Symptoms reported: itching · the patient reports the lesion is raised or bumpy · this is a close-up image · female contributor, age 30–39 · reported duration is less than one week · self-categorized by the patient as a rash · skin tone: lay reviewers estimated Monk skin tone scale 2 or 3 (two reviewer pools) · the affected area is the front of the torso and back of the torso: 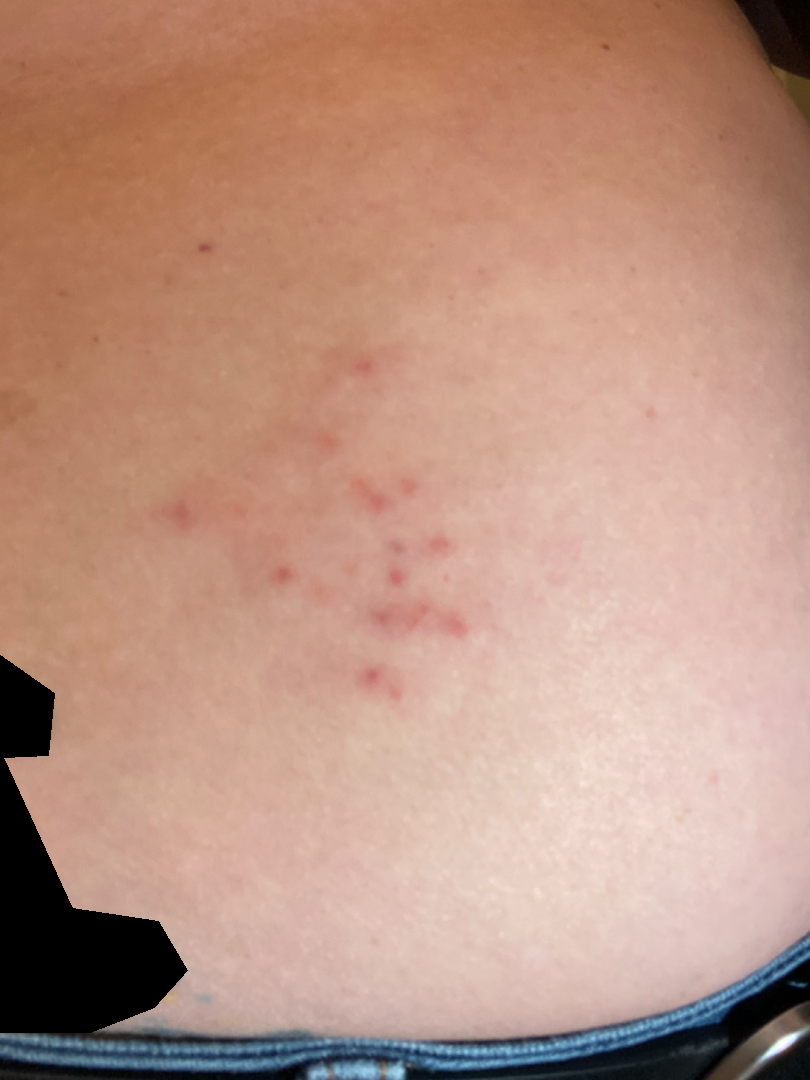| feature | finding |
|---|---|
| assessment | not assessable |